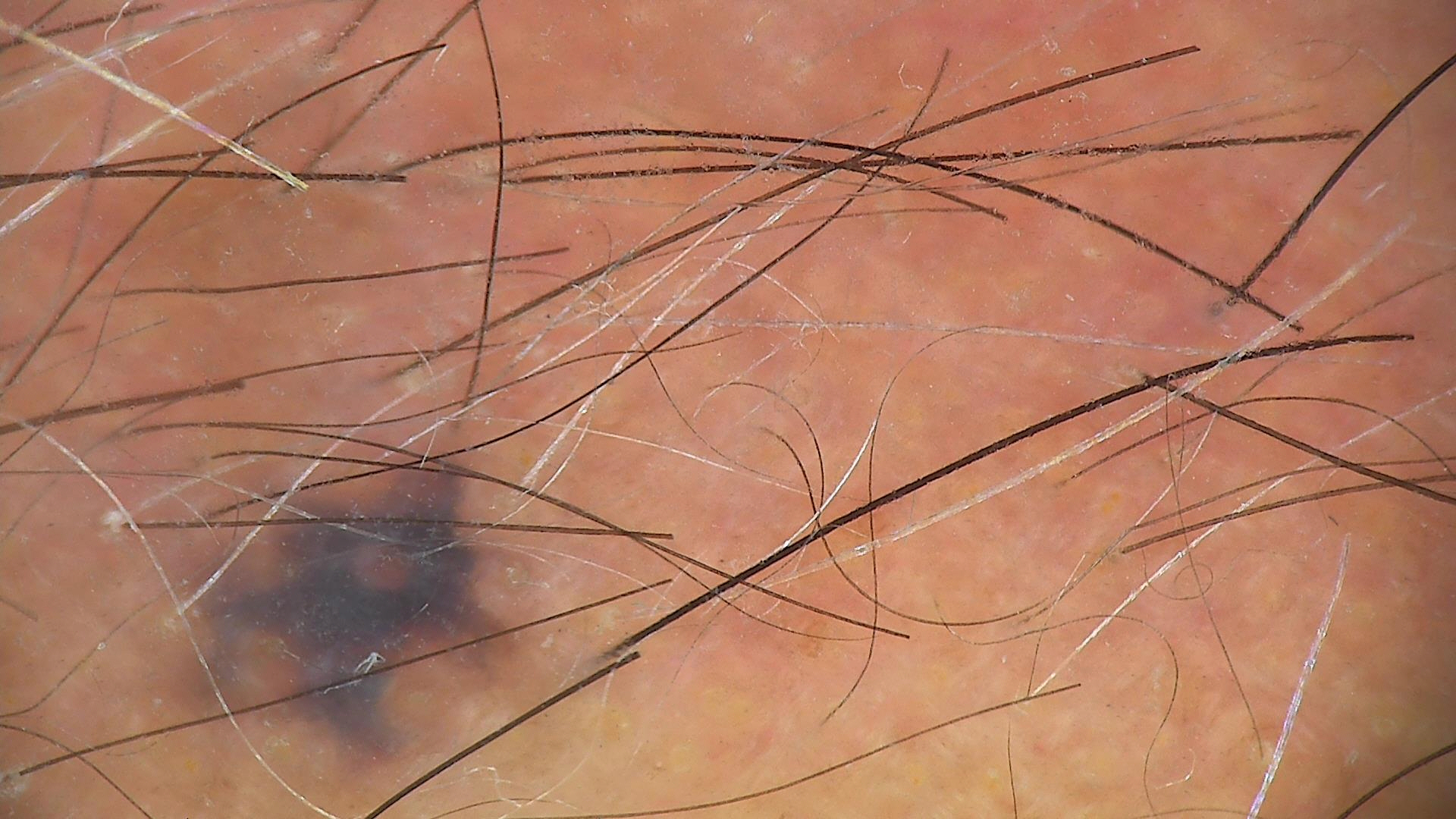Histopathologically confirmed as a lentigo maligna.